The patient is Fitzpatrick skin type II; a skin lesion imaged with contact-polarized dermoscopy; a female patient in their mid-20s: 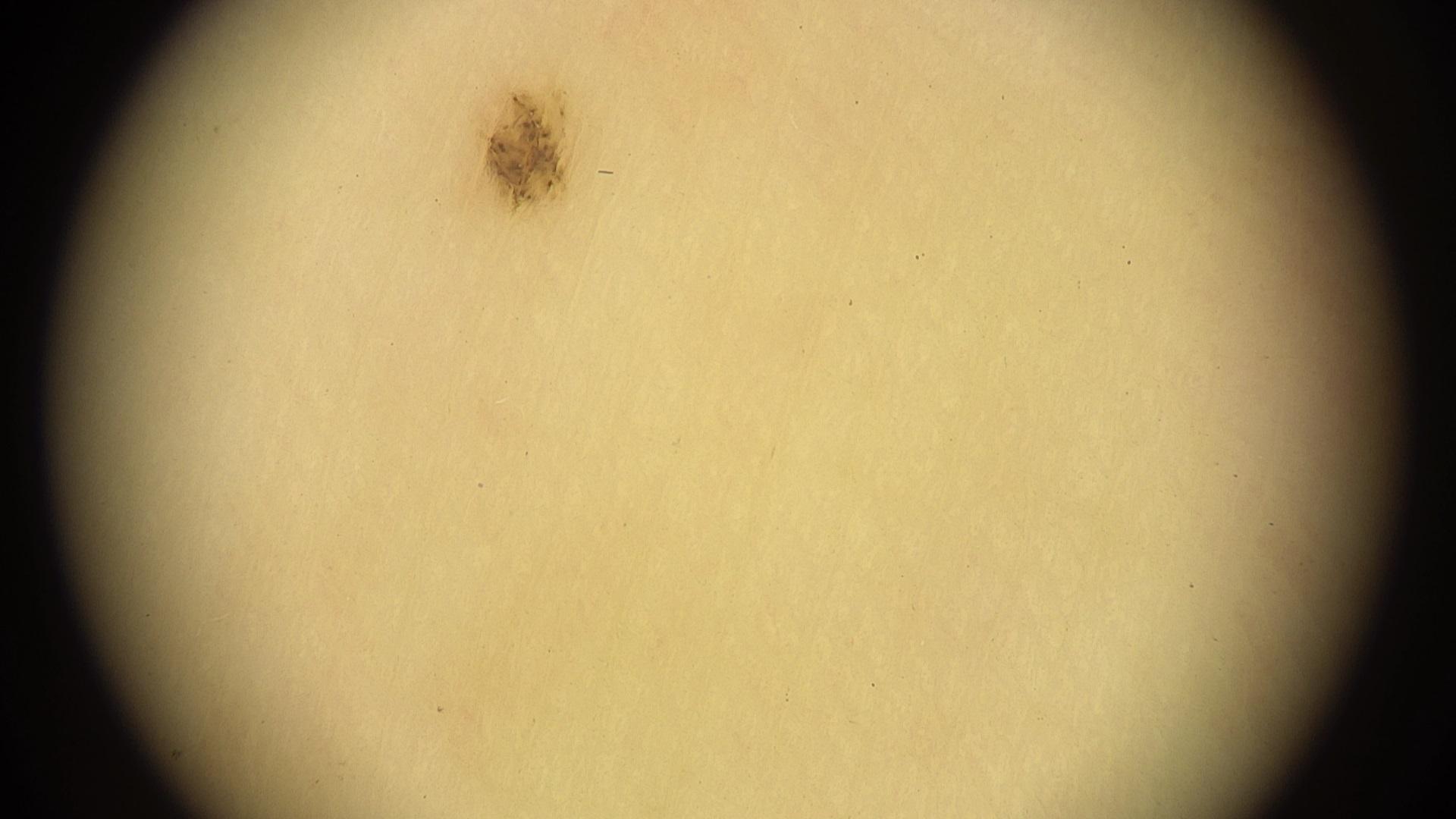Summary:
The lesion involves a lower extremity.
Assessment:
Expert review favored a lesion of melanocytic lineage — a nevus.